A skin lesion imaged with a dermatoscope. A male subject roughly 55 years of age: 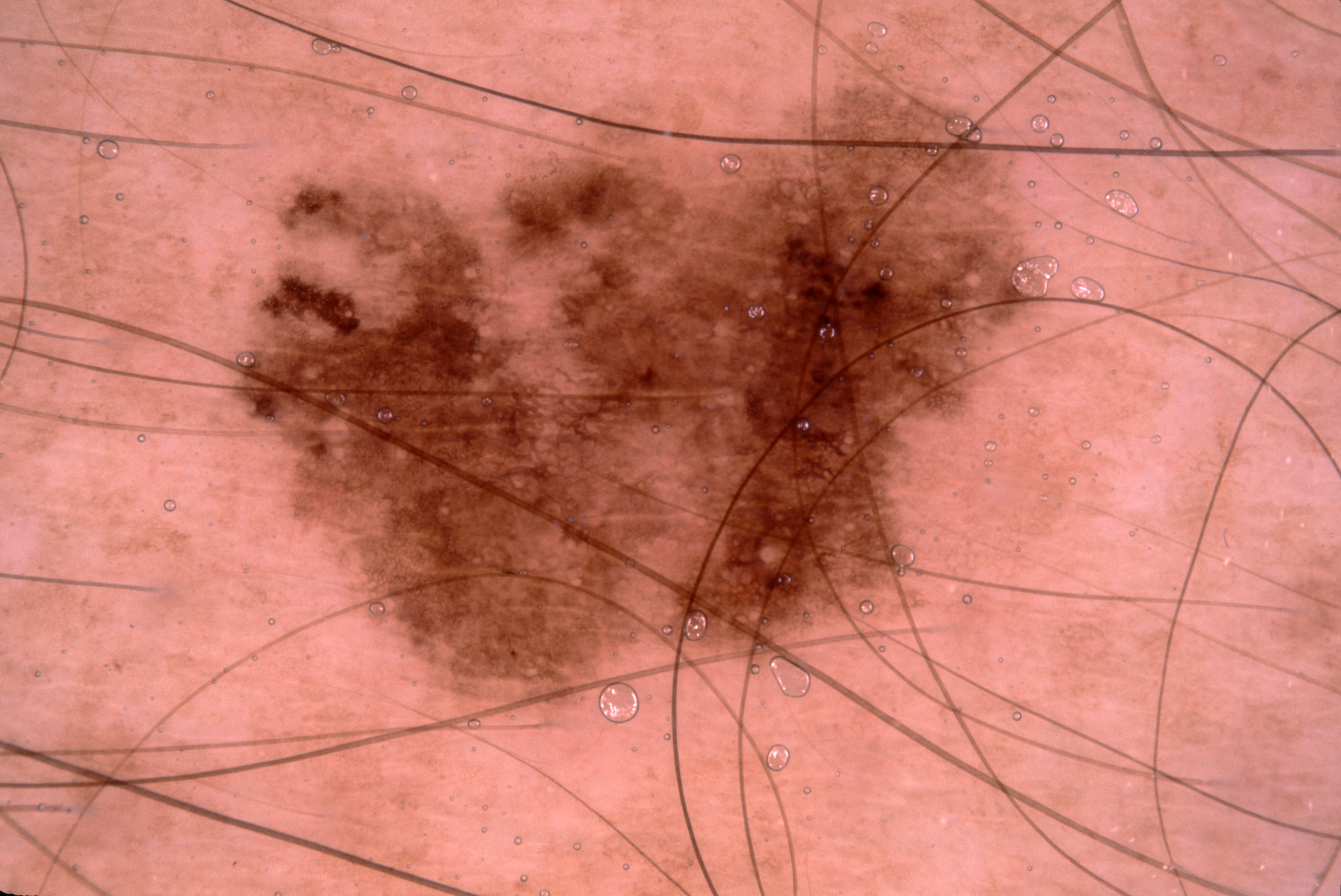Image and clinical context: Dermoscopic examination shows pigment network. With coordinates (x1, y1, x2, y2), the lesion occupies the region 241 91 1027 707. Conclusion: Histopathologically confirmed as a melanoma.